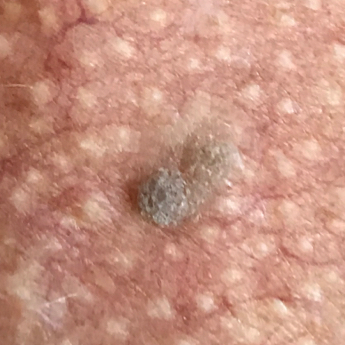Case summary:
A subject age 73. A smartphone photograph of a skin lesion. Located on the chest. The patient reports that the lesion has grown and is elevated.
Impression:
Clinically diagnosed as a benign skin lesion — a seborrheic keratosis.